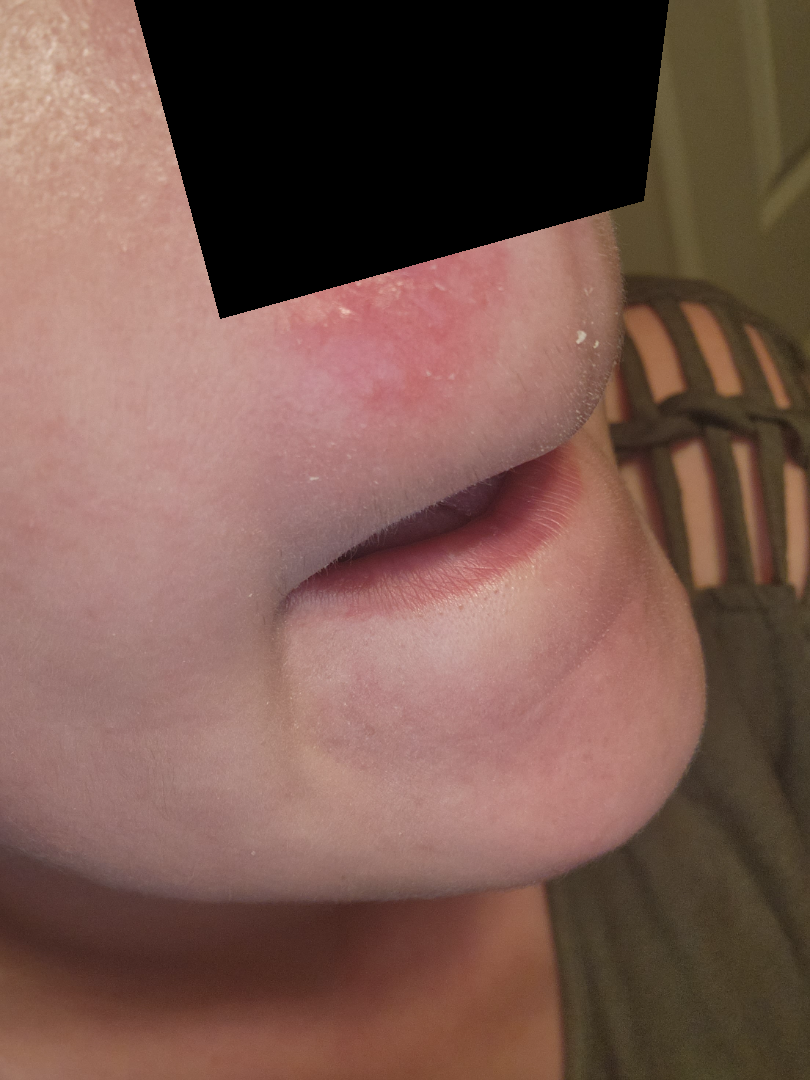<report>
<patient_category>a rash</patient_category>
<duration>one to four weeks</duration>
<systemic_symptoms>none reported</systemic_symptoms>
<symptoms>itching</symptoms>
<shot_type>at an angle</shot_type>
<patient>female, age 30–39</patient>
<body_site>head or neck</body_site>
<texture>rough or flaky</texture>
<differential>
  <leading>Perioral Dermatitis</leading>
  <unlikely>Herpes Simplex, Seborrheic Dermatitis</unlikely>
</differential>
</report>